The photograph is a close-up of the affected area: 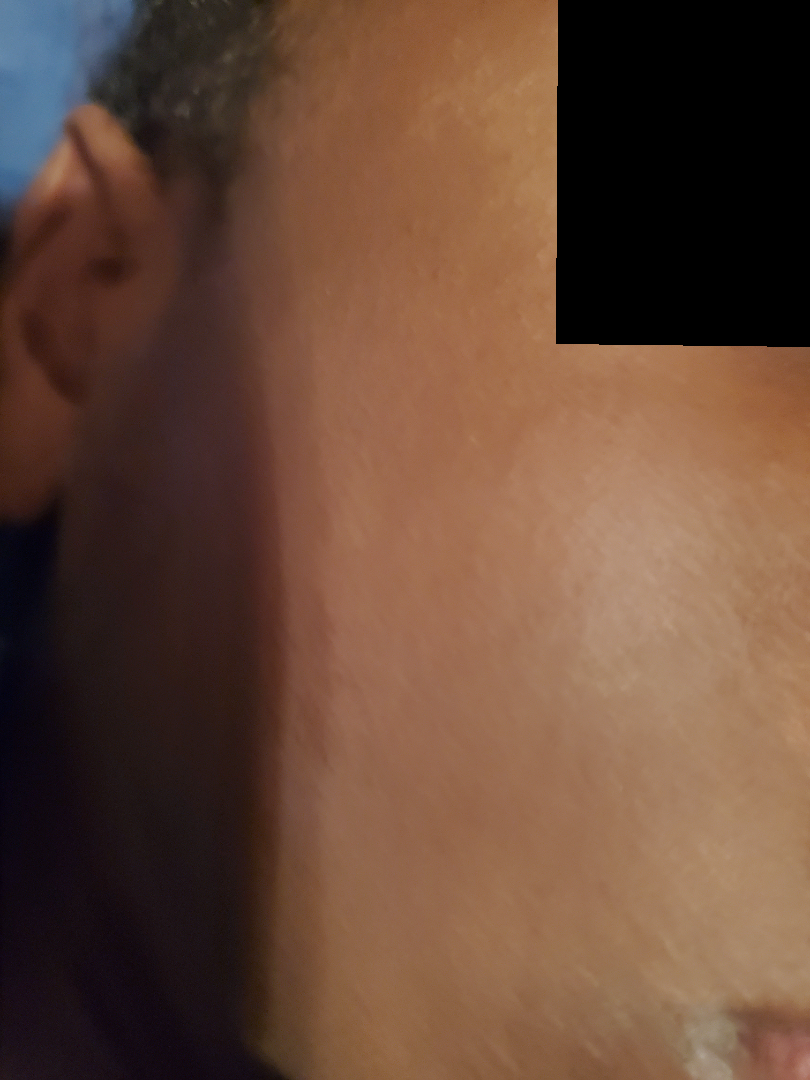The skin findings could not be characterized from the image.